Dermoscopy of a skin lesion.
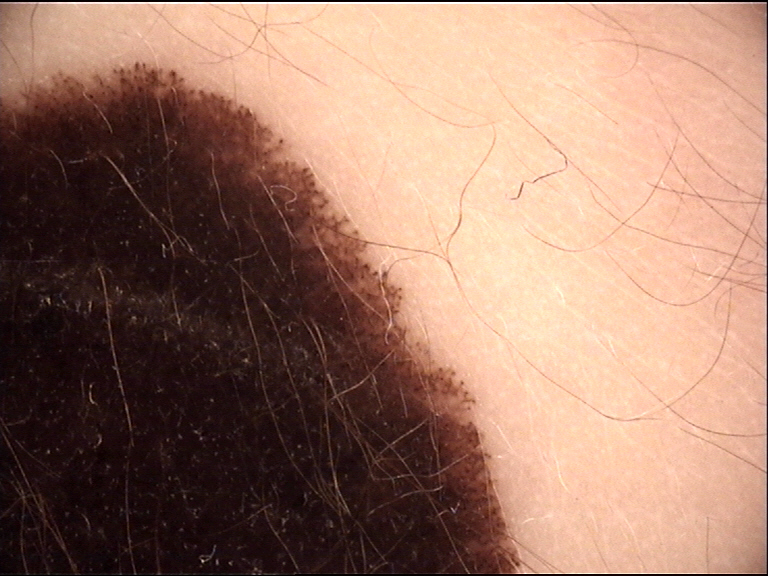<lesion>
  <diagnosis>
    <name>congenital compound nevus</name>
    <code>ccb</code>
    <malignancy>benign</malignancy>
    <super_class>melanocytic</super_class>
    <confirmation>expert consensus</confirmation>
  </diagnosis>
</lesion>